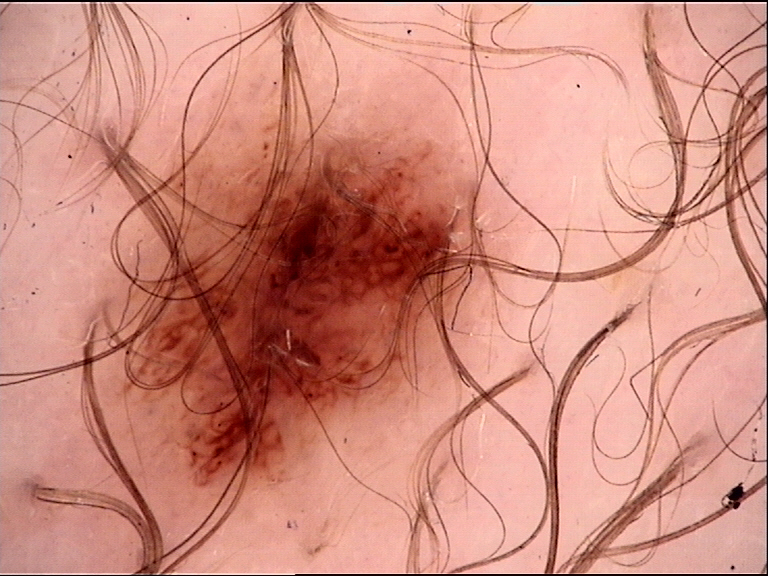Impression: The diagnosis was a benign lesion — a dysplastic junctional nevus.